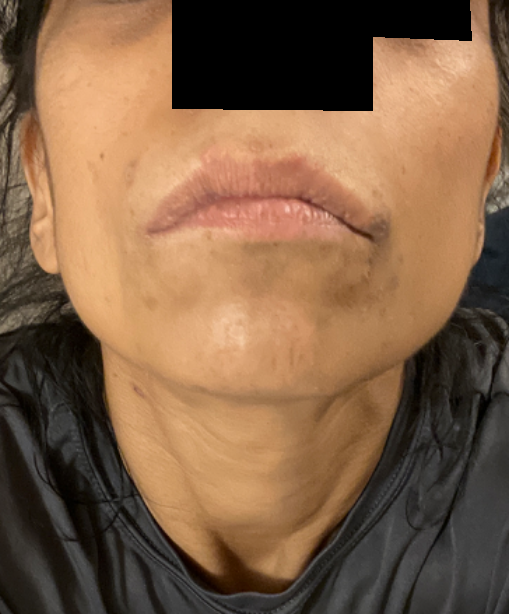* patient-reported symptoms · bothersome appearance
* other reported symptoms · none reported
* view · at a distance
* body site · head or neck and back of the torso
* patient's own categorization · a rash
* surface texture · fluid-filled and raised or bumpy
* onset · one to three months
* contributor · female, age 30–39
* clinical impression · Perioral Dermatitis (most likely); Acne (possible)